A dermoscopic view of a skin lesion:
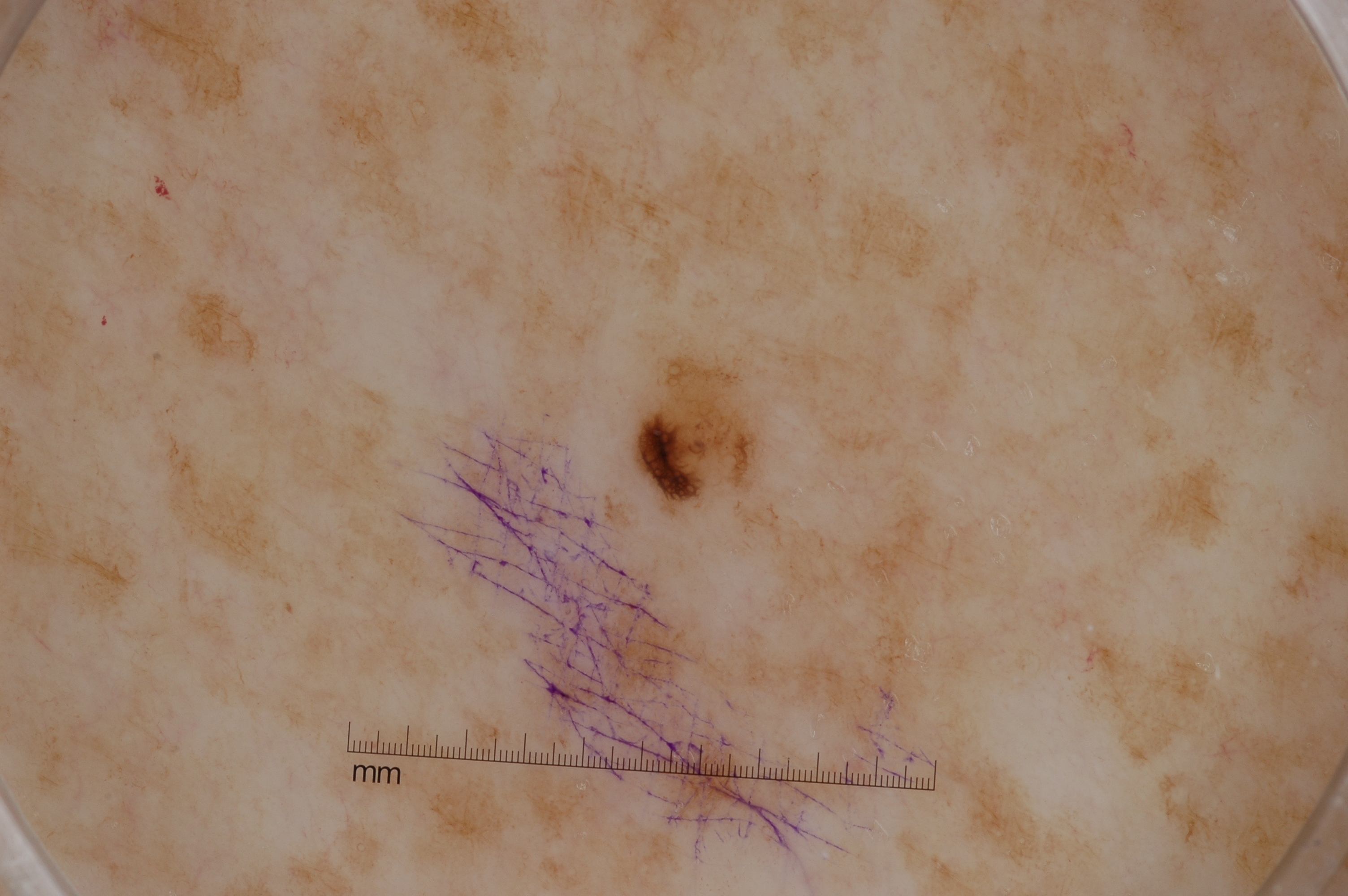| feature | finding |
|---|---|
| lesion size | small |
| lesion location | 622, 350, 758, 511 |
| dermoscopic pattern | pigment network |
| impression | a melanocytic nevus |